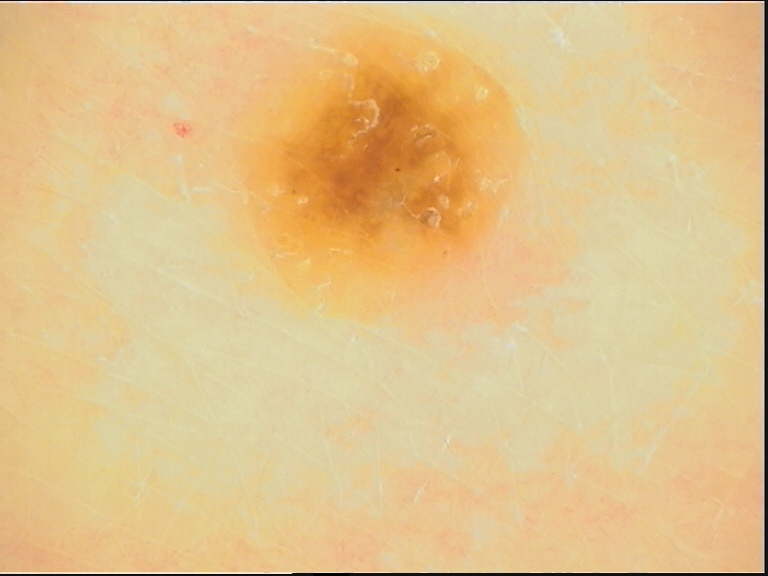Case: A dermoscopy image of a single skin lesion. The architecture is that of a keratinocytic lesion. Impression: Diagnosed as a benign lesion — a seborrheic keratosis.